An image taken at an angle. The affected area is the leg, front of the torso and arm:
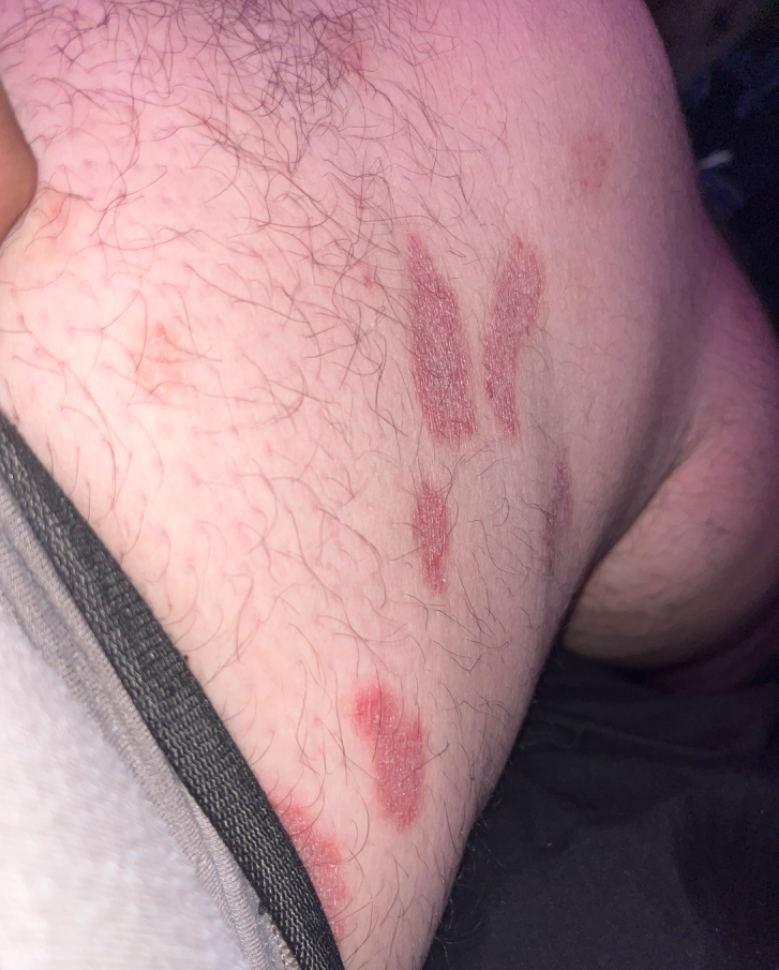A single dermatologist reviewed the case: most consistent with Psoriasis.